Close-up view · the patient is a female aged 40–49.
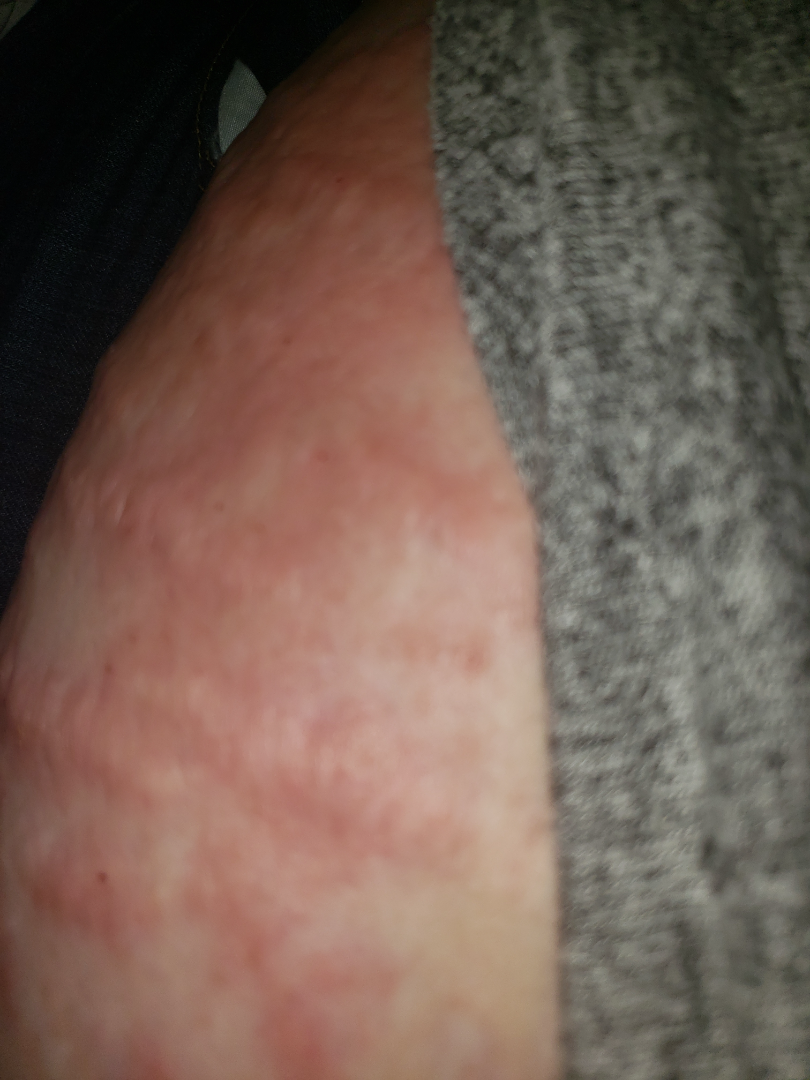{"assessment": "indeterminate", "symptoms": ["enlargement", "itching"], "patient_category": "a rash", "duration": "one to four weeks", "texture": "raised or bumpy", "systemic_symptoms": "none reported"}